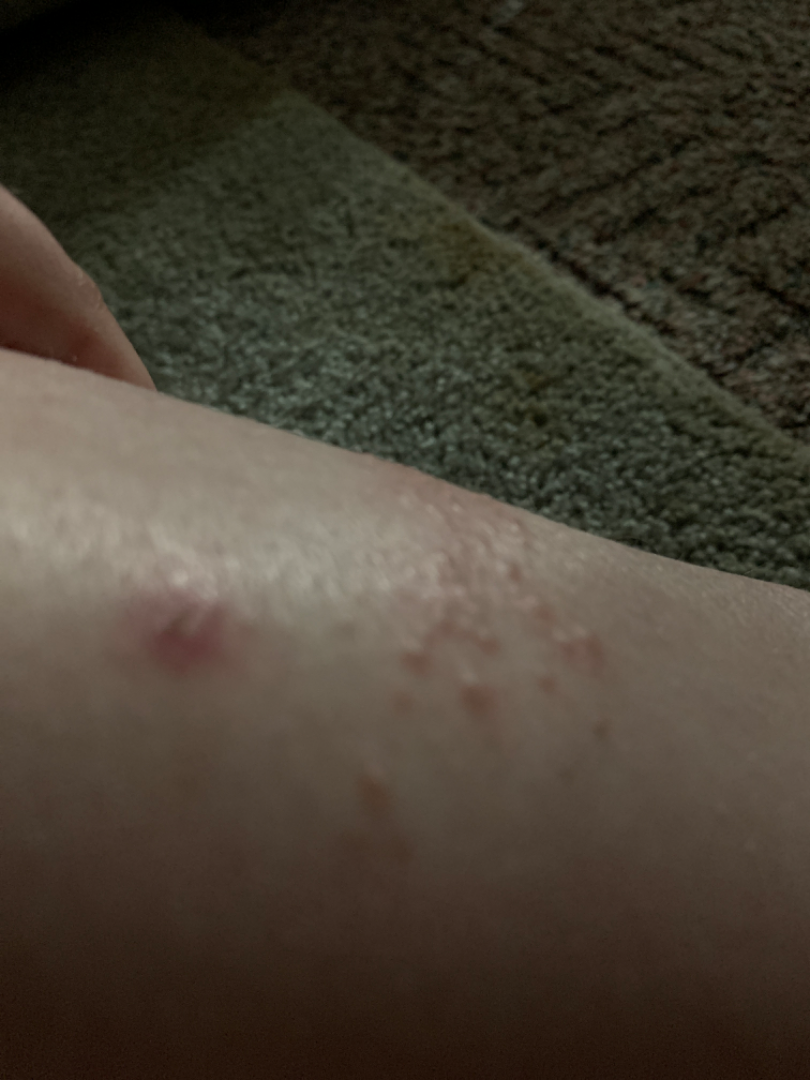  assessment: unable to determine